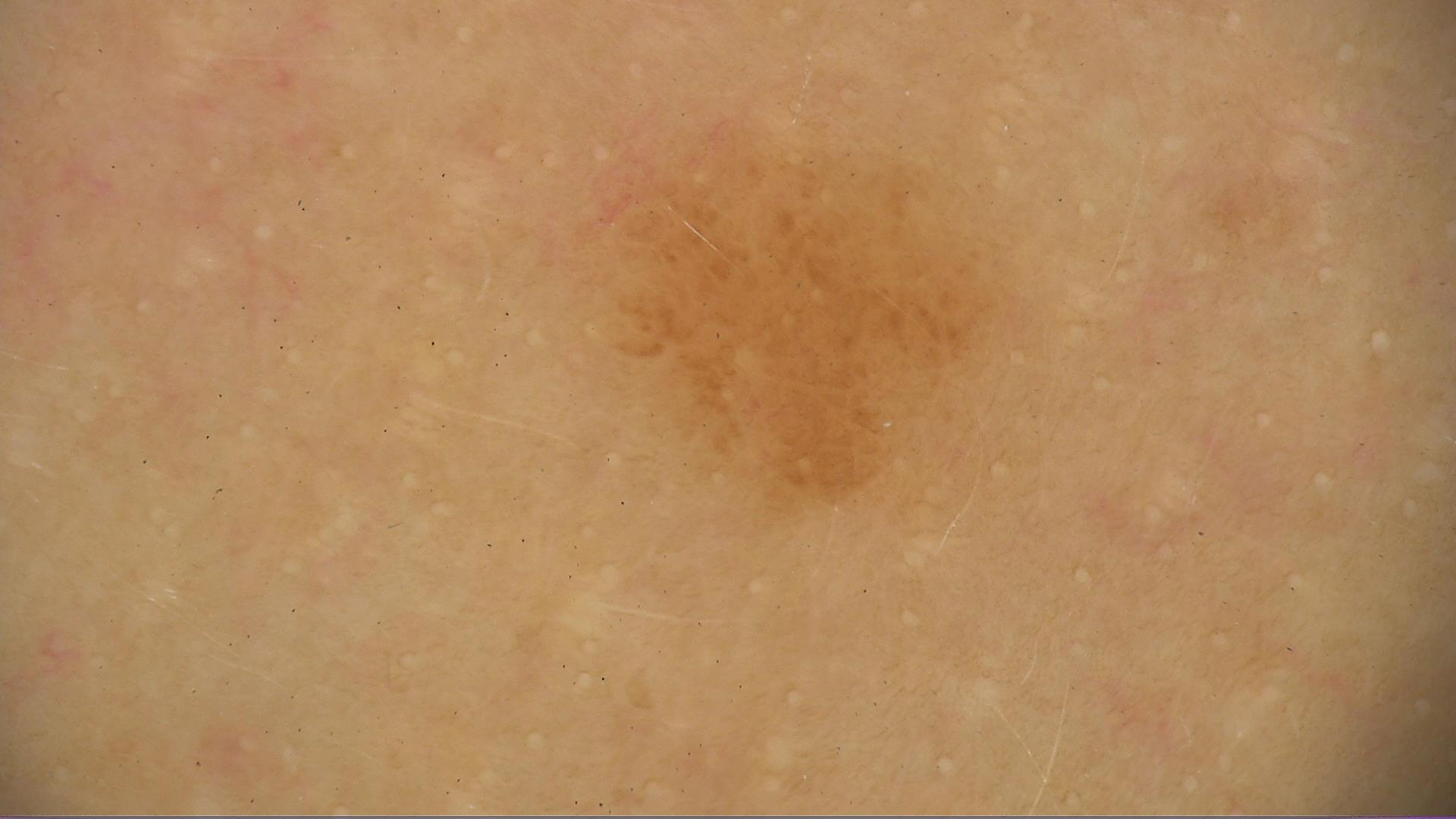A dermoscopic photograph of a skin lesion.
This is a banal lesion.
Labeled as a junctional nevus.